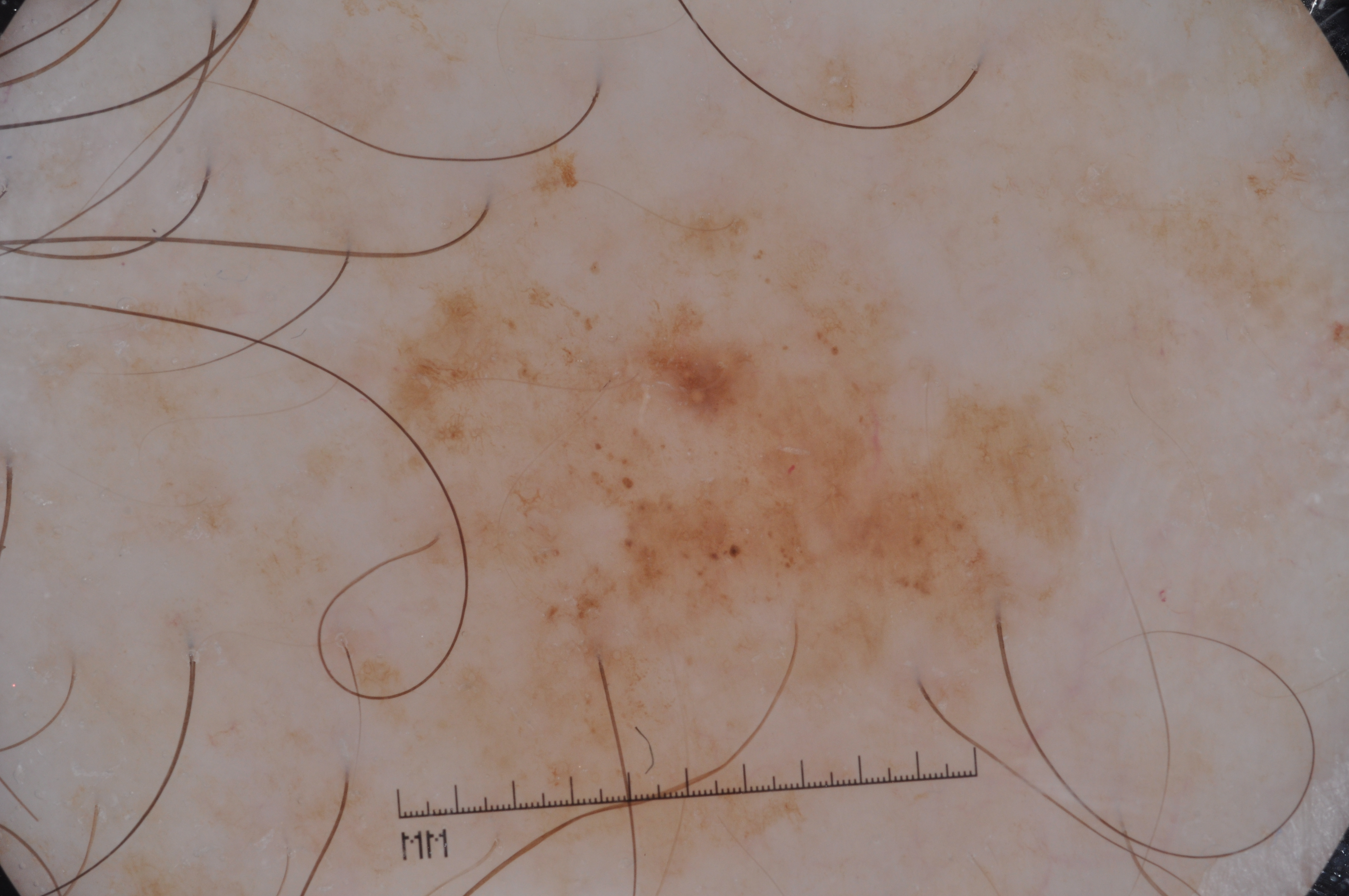Findings: This is a dermoscopic photograph of a skin lesion. With coordinates (x1, y1, x2, y2), the lesion spans bbox=[371, 114, 1106, 877]. Dermoscopy demonstrates milia-like cysts and pigment network, with no negative network or streaks. Conclusion: Histopathological examination showed a melanoma, a malignant skin lesion.